An image taken at a distance · the lesion involves the arm · the subject is female.
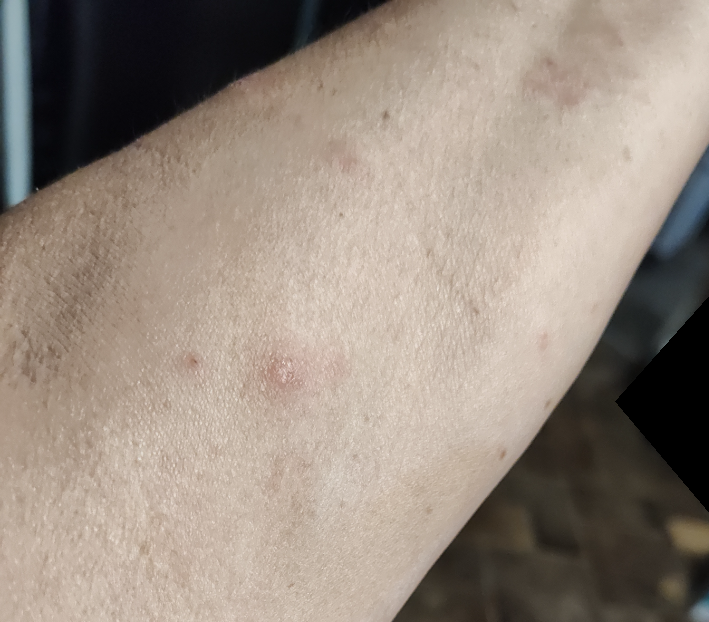- diagnostic considerations · the differential, in no particular order, includes Granuloma annulare, Skin and soft tissue atypical mycobacterial infection, Eczema and Allergic Contact Dermatitis